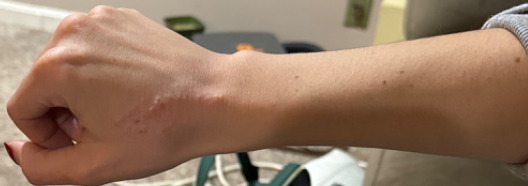  body_site:
    - arm
    - back of the hand
  patient_category: a rash
  texture: raised or bumpy
  shot_type: at a distance
  symptoms:
    - bothersome appearance
    - enlargement
    - itching
  duration: less than one week
  patient: female, age 18–29
  systemic_symptoms: none reported
  skin_tone:
    monk_skin_tone:
      - 3
      - 4
  differential:
    tied_lead:
      - Impetigo
      - Herpes Zoster
      - Herpes Simplex